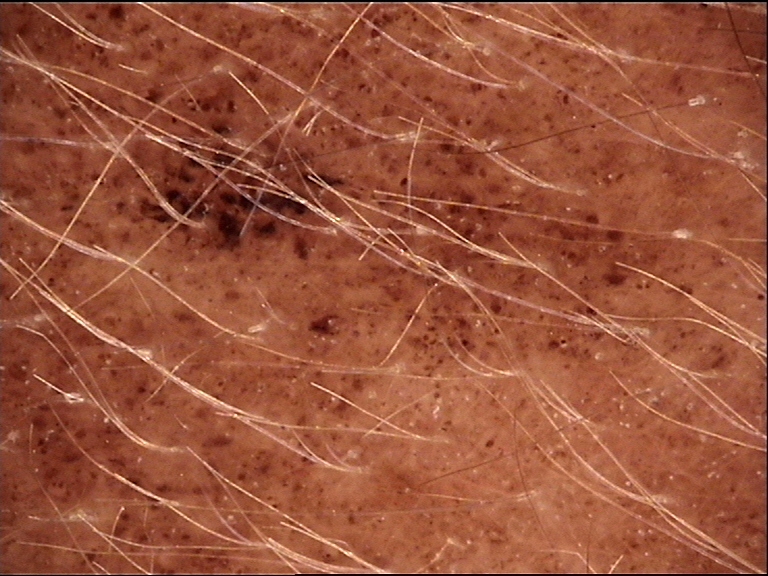image type = dermoscopy, subtype = banal, class = congenital compound nevus (expert consensus).